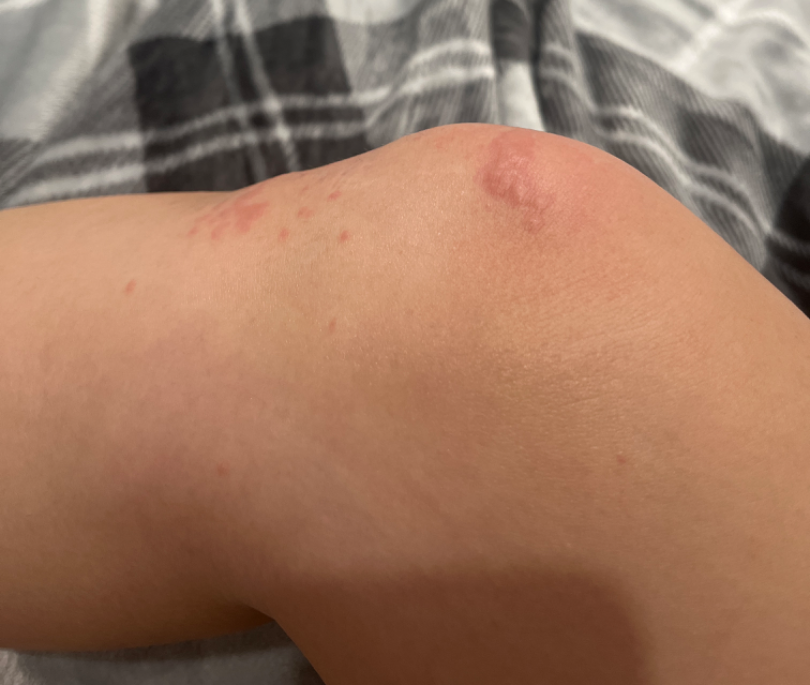The reviewer was unable to grade this case for skin condition. The photograph was taken at an angle.